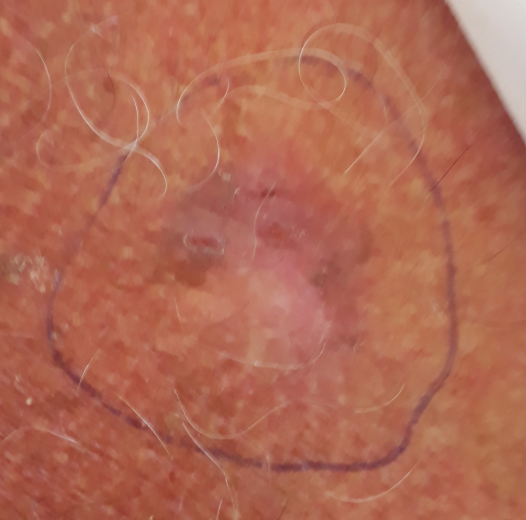subject: male, 72 years old
region: the chest
symptoms: elevation, itching, bleeding, growth / no pain, no change in appearance
diagnosis: basal cell carcinoma (biopsy-proven)